The patient says their skin reddens with sun exposure · by self-report, no family history of skin cancer · a male subject age 62 · dermoscopy of a skin lesion · the patient describes having few moles overall: 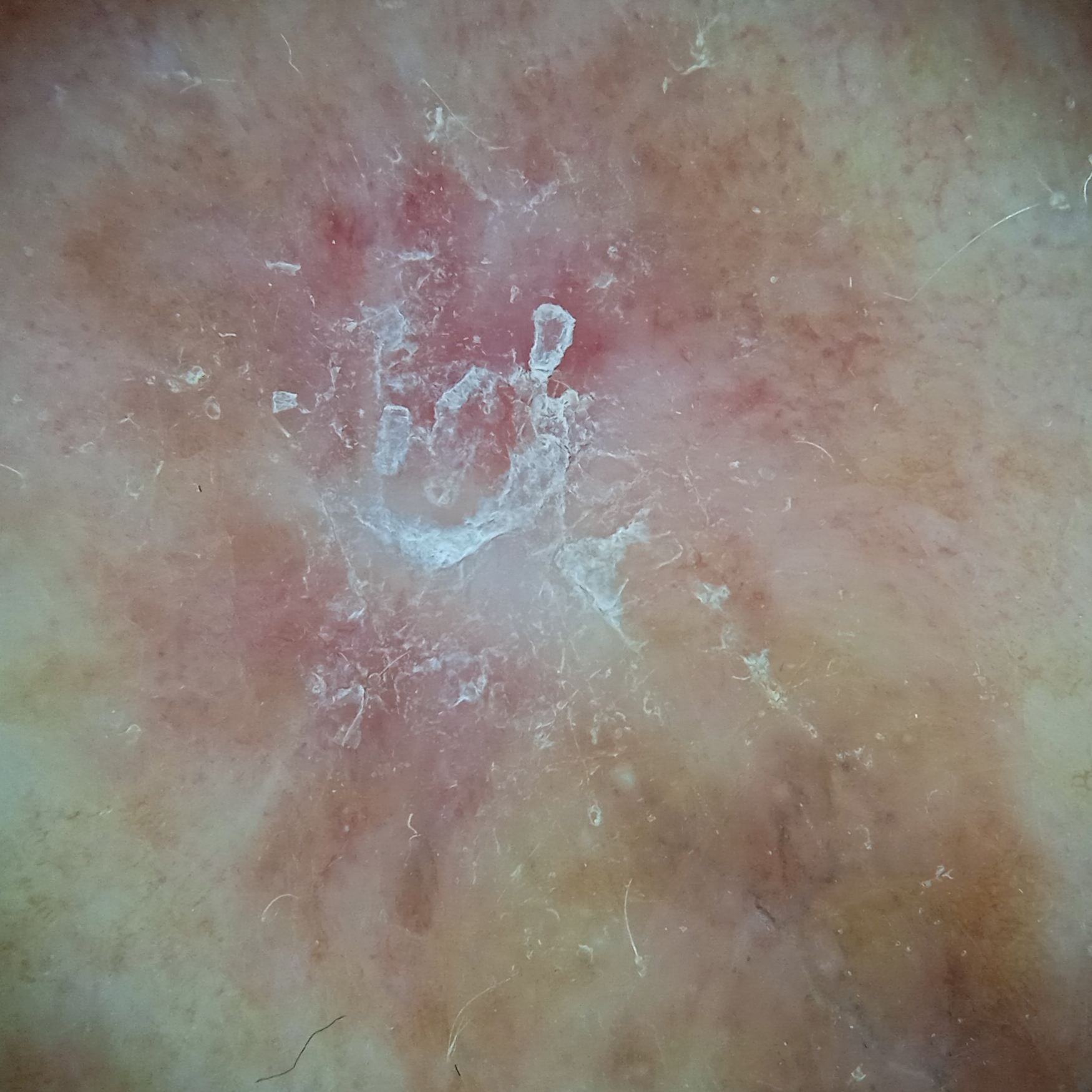Assessment:
The consensus diagnosis for this lesion was a squamous cell carcinoma.